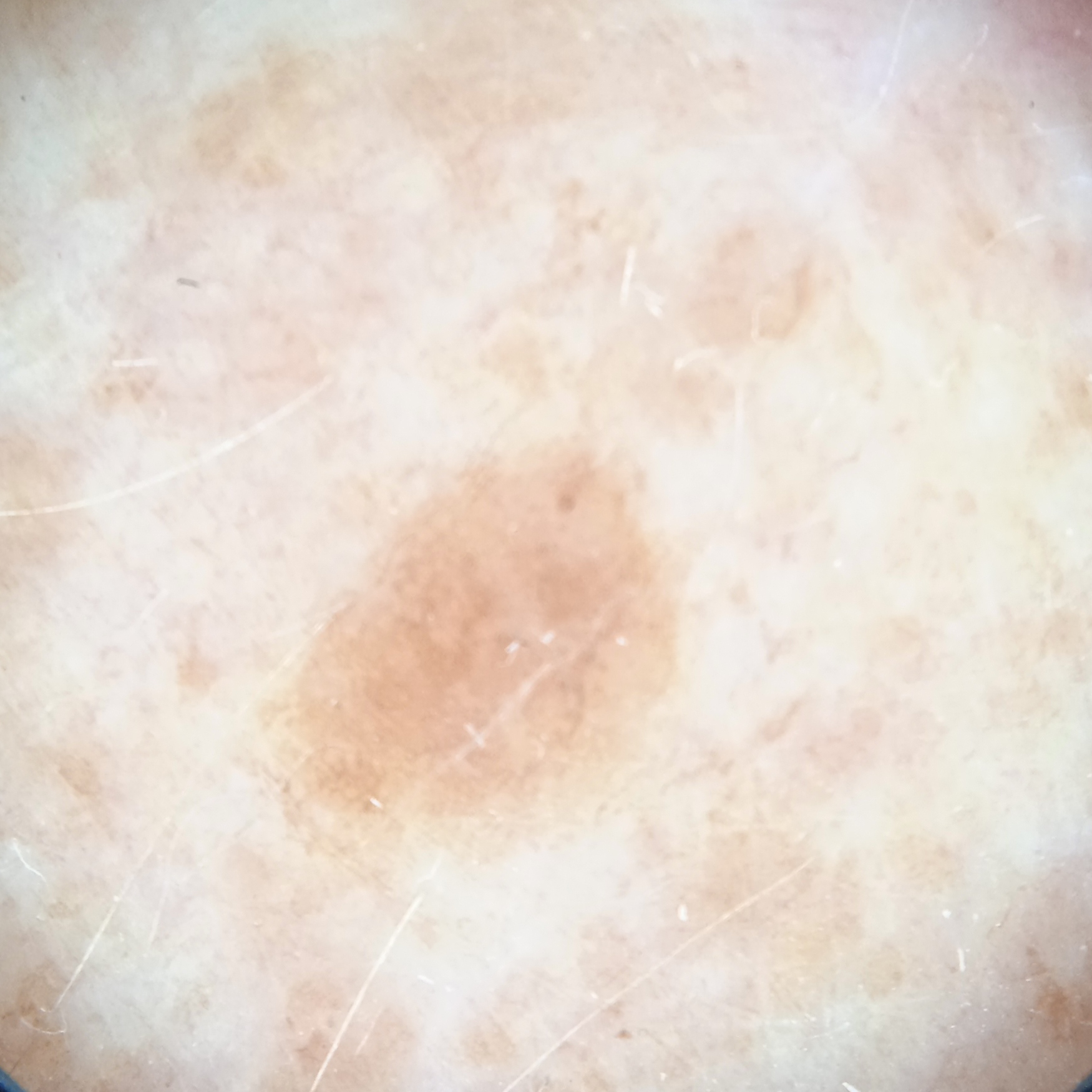Case:
– nevus count · numerous melanocytic nevi
– image · dermatoscopic image
– referral · research study (no referral diagnosis)
– patient · female, 78 years of age
– diagnosis · seborrheic keratosis (dermatologist consensus)